A dermoscopic close-up of a skin lesion.
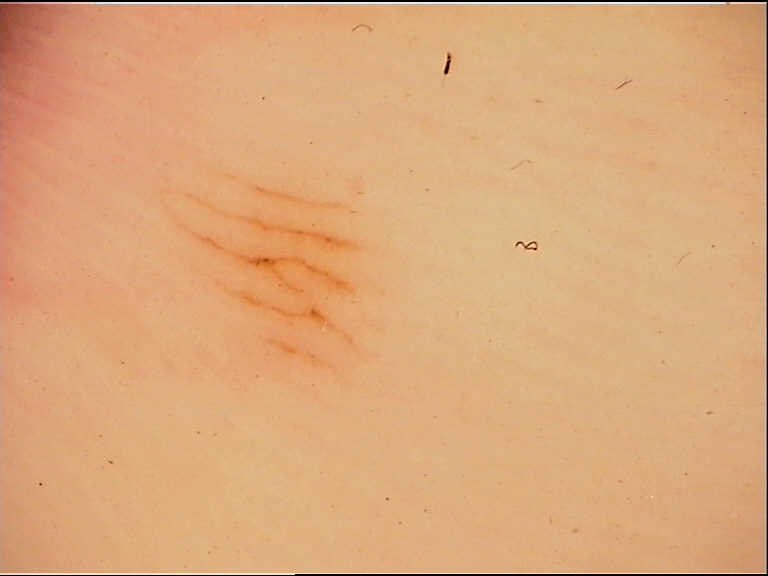This is a banal lesion. Diagnosed as an acral junctional nevus.